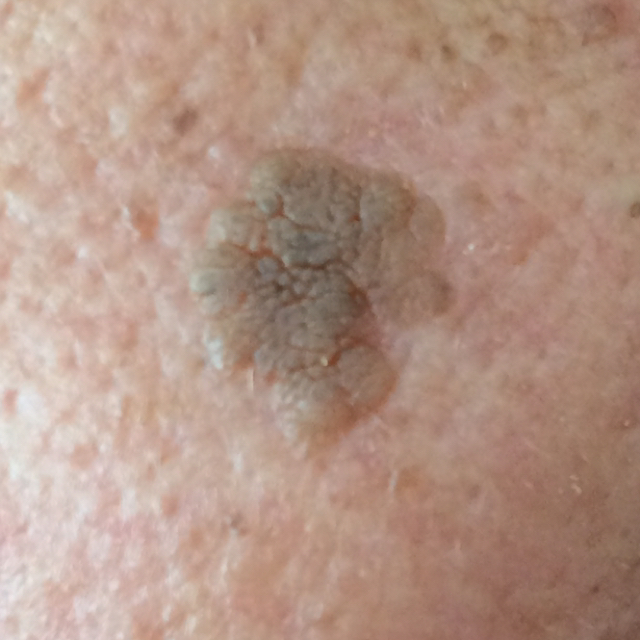Clinical context:
A subject aged 43. A clinical photograph of a skin lesion. The patient describes that the lesion has grown, is elevated, and itches.
Impression:
Expert review favored a seborrheic keratosis.